The photo was captured at an angle.
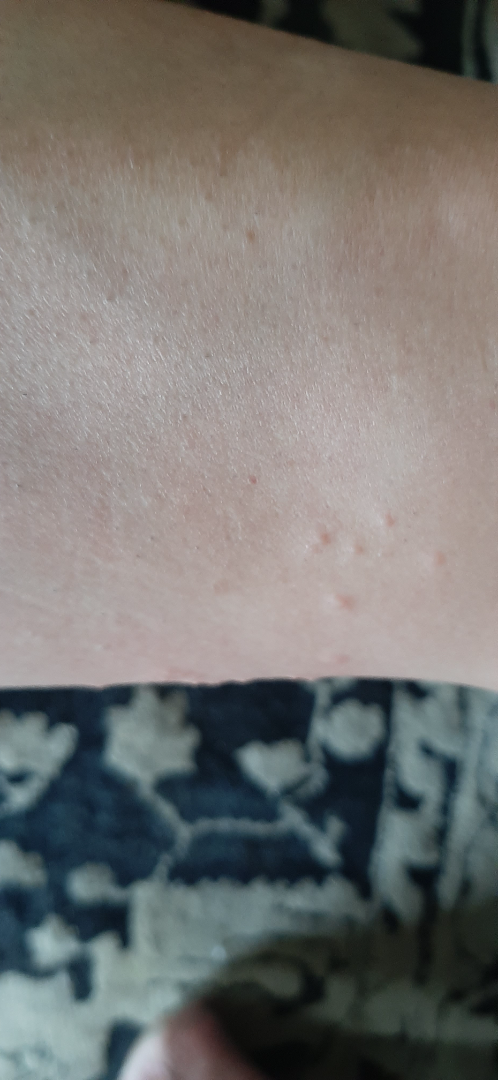{
  "differential": {
    "leading": [
      "Insect Bite"
    ],
    "considered": [
      "Allergic Contact Dermatitis"
    ],
    "unlikely": [
      "Molluscum Contagiosum"
    ]
  }
}